The patient is a female aged approximately 45. A dermoscopic view of a skin lesion.
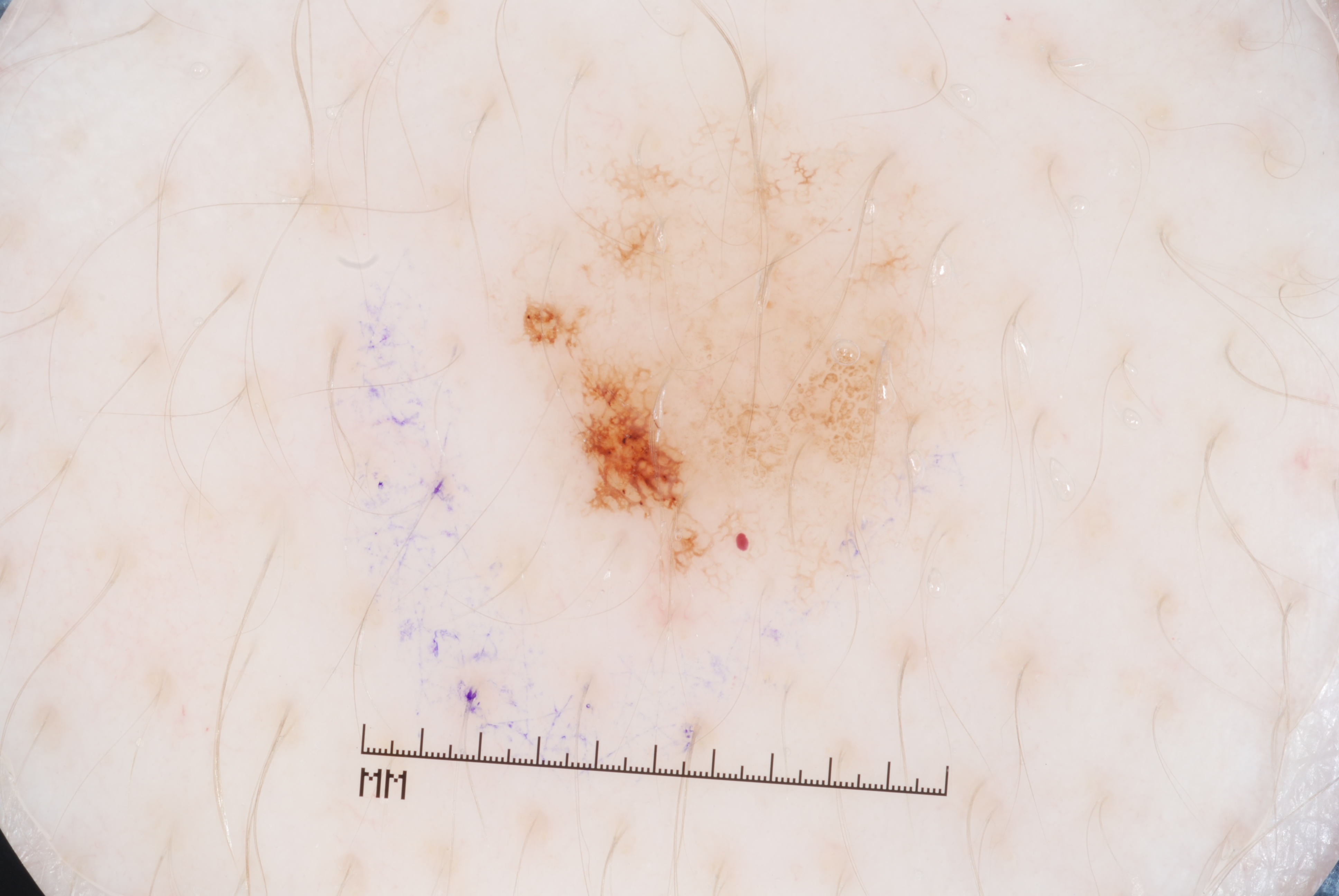Q: How much of the field does the lesion occupy?
A: moderate
Q: Where is the lesion in the image?
A: 513/105/941/581
Q: What does dermoscopy show?
A: pigment network
Q: What is the diagnosis?
A: a melanocytic nevus